Close-up view.
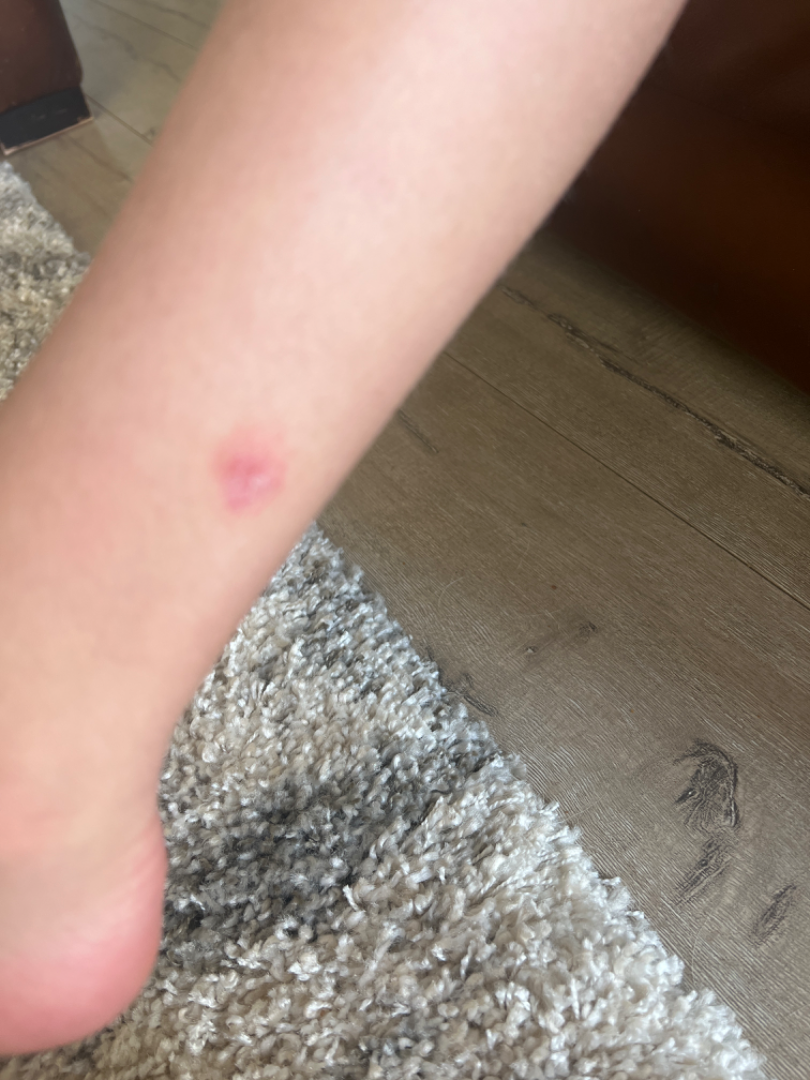| key | value |
|---|---|
| assessment | not assessable |